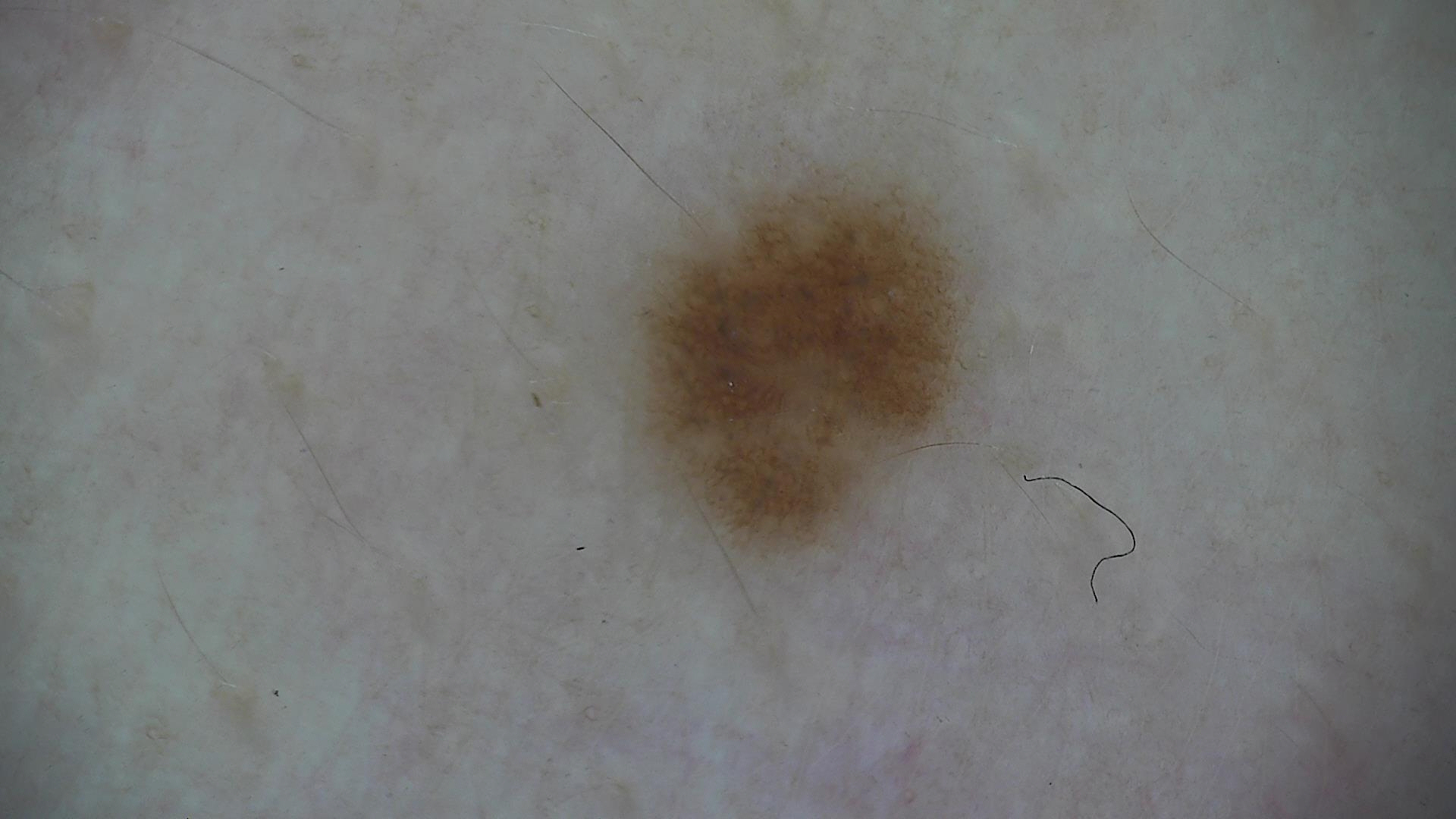| key | value |
|---|---|
| diagnostic label | dysplastic junctional nevus (expert consensus) |